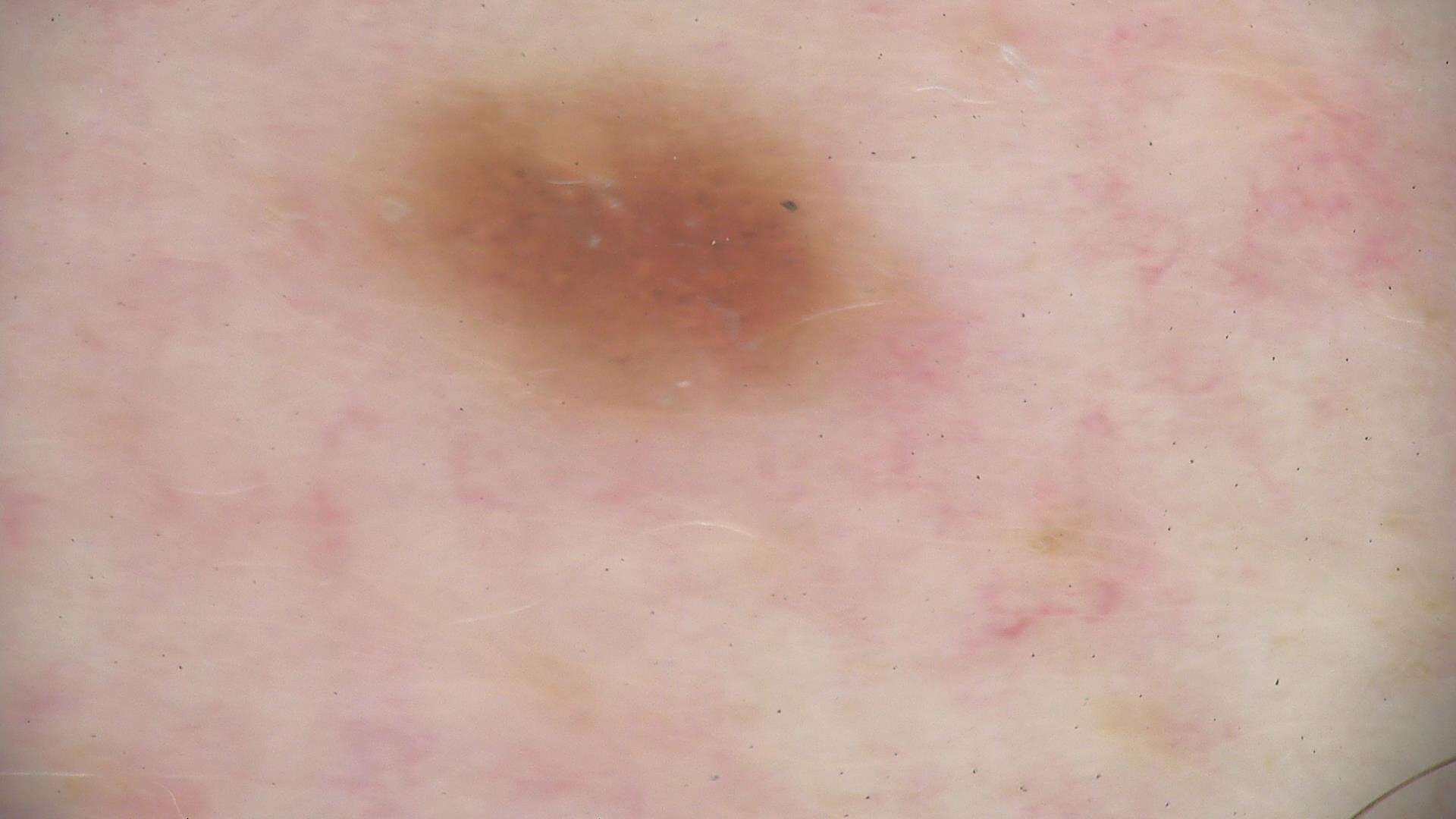The diagnosis was a dysplastic junctional nevus.